By self-report, a family history of skin cancer, a personal history of skin cancer, and immunosuppression · the patient says their skin reddens painfully with sun exposure · a dermoscopy image of a skin lesion · imaged for a research study, with no referral diagnosis recorded · numerous moles by the patient's own estimate · a male subject age 65.
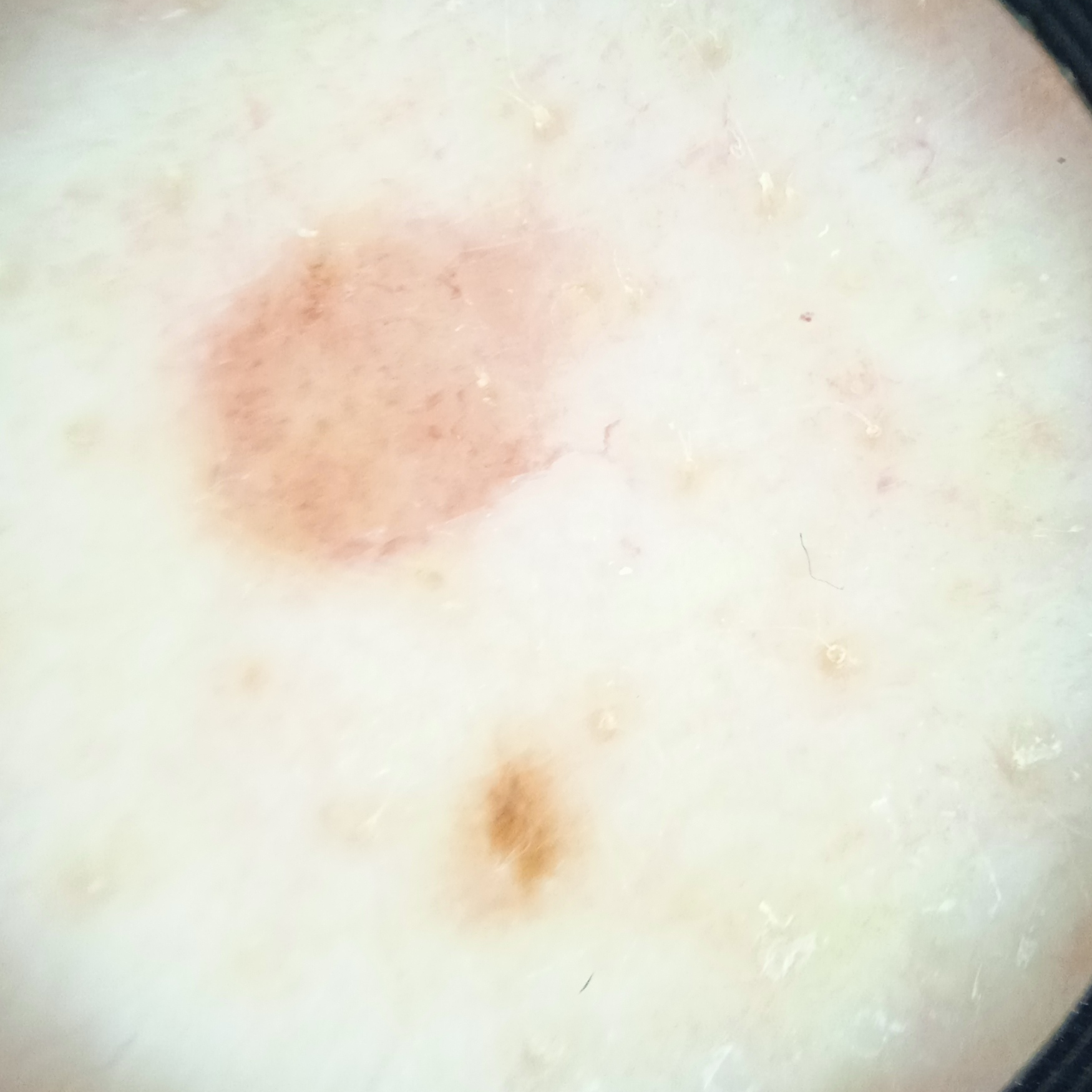– lesion size · 4.4 mm
– assessment · melanocytic nevus (dermatologist consensus)